A dermoscopic image of a skin lesion · the patient says their skin tans without first burning · the patient describes having a moderate number of moles · a female patient 58 years of age · by self-report, a personal history of skin cancer, a family history of skin cancer, and a personal history of cancer · acquired for a research image collection, with no referral diagnosis:
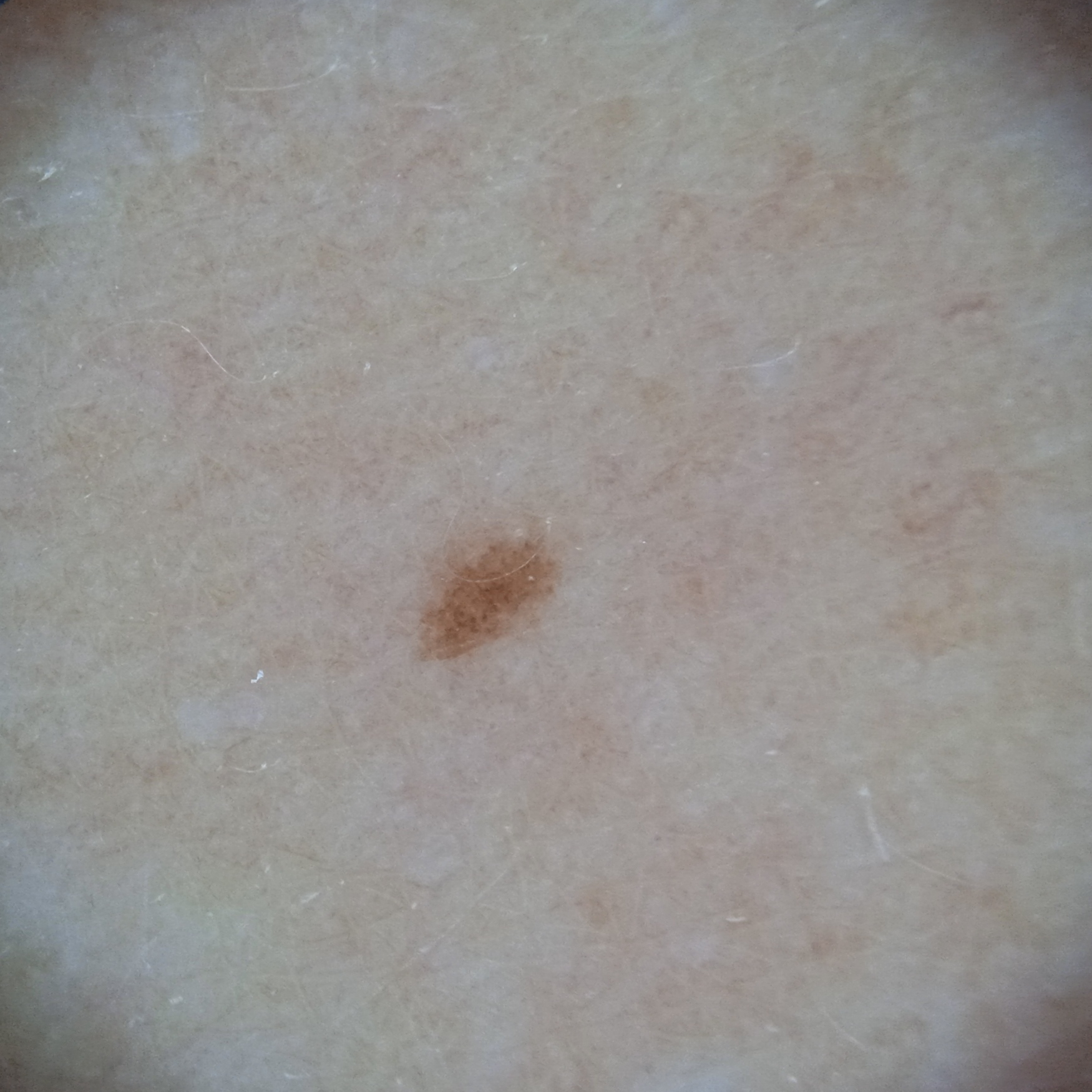{"lesion_location": "an arm", "lesion_size": {"diameter_mm": 1.9}, "diagnosis": {"name": "melanocytic nevus", "malignancy": "benign"}}